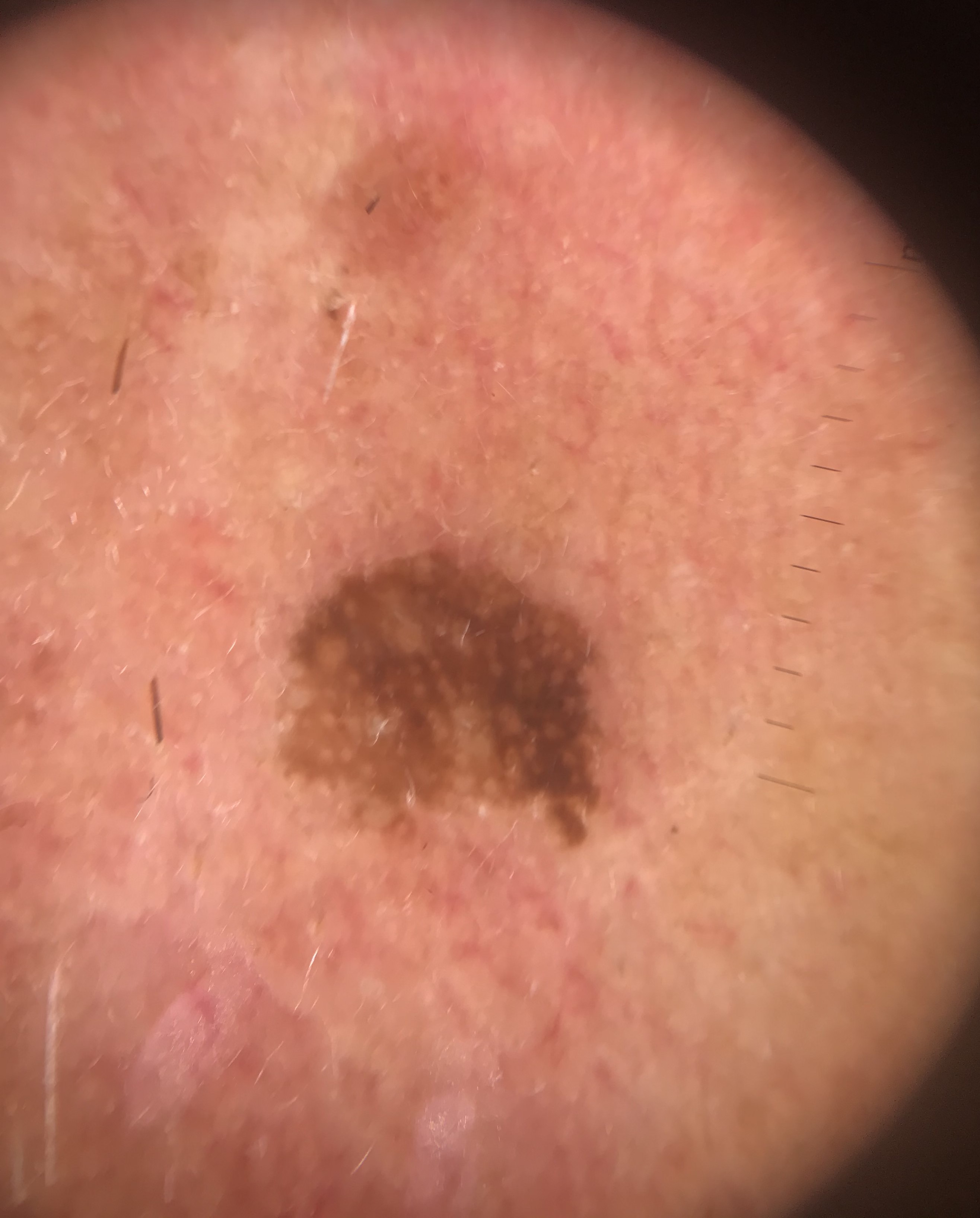modality: dermoscopy
assessment: seborrheic keratosis (expert consensus)